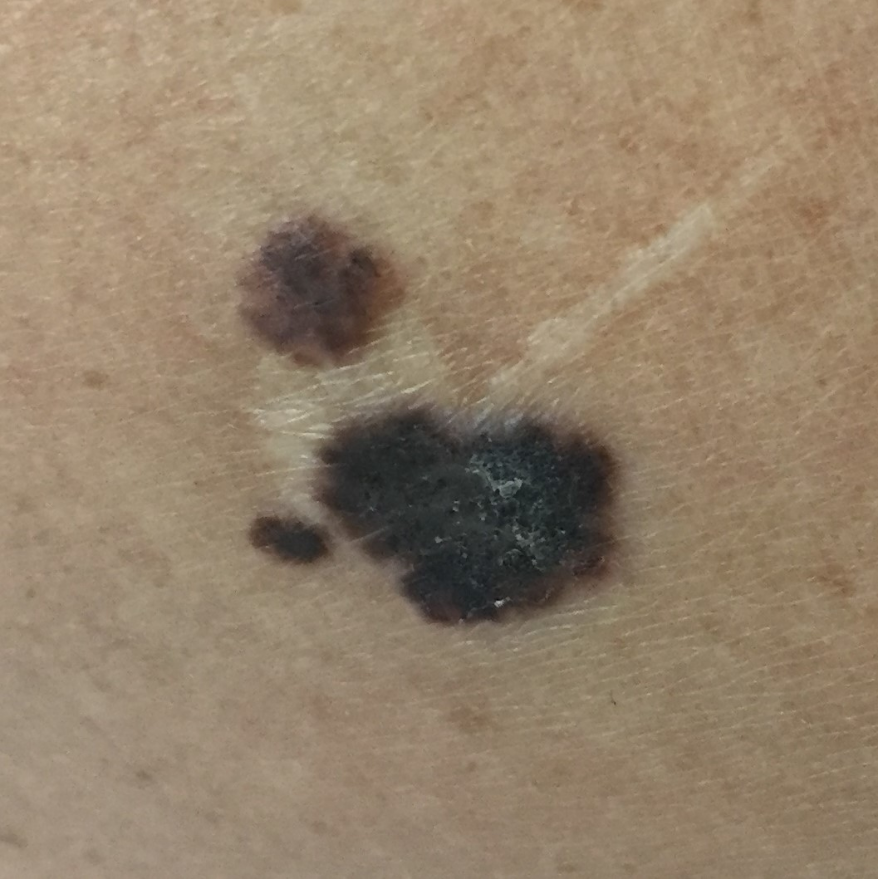A clinical photograph showing a skin lesion. Fitzpatrick phototype II. A female subject aged 49. The lesion was found on a thigh. The lesion measures approximately 23 × 20 mm. Per patient report, the lesion has changed, has grown, and is elevated. Histopathology confirmed a malignant skin lesion — a melanoma.